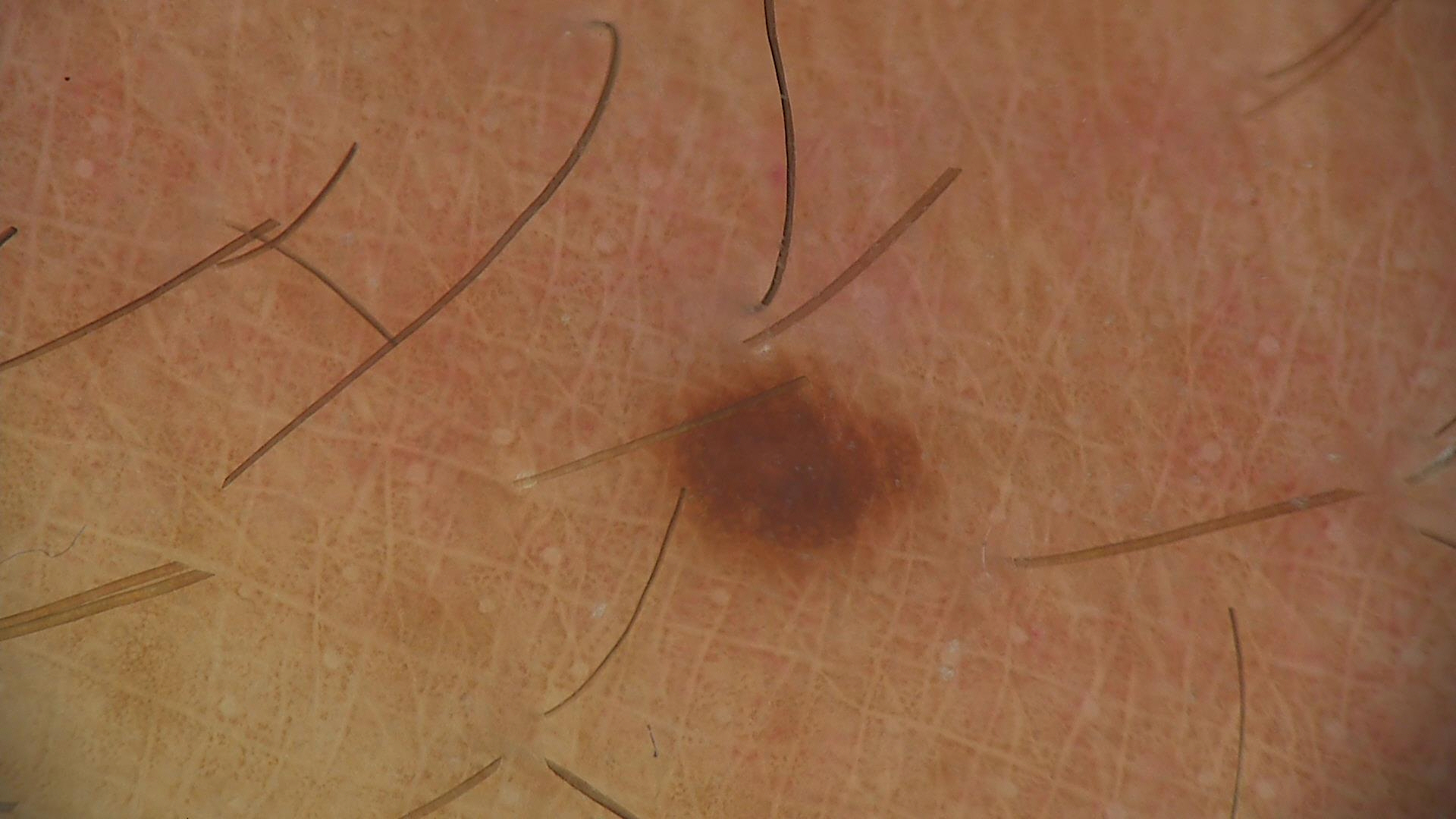| field | value |
|---|---|
| modality | dermoscopy |
| diagnosis | junctional nevus (expert consensus) |